The patient described the issue as a rash. Reported duration is less than one week. The subject is a male aged 50–59. The patient indicates the lesion is fluid-filled, raised or bumpy and rough or flaky. Symptoms reported: pain and burning. The patient indicates associated fatigue. Close-up view: 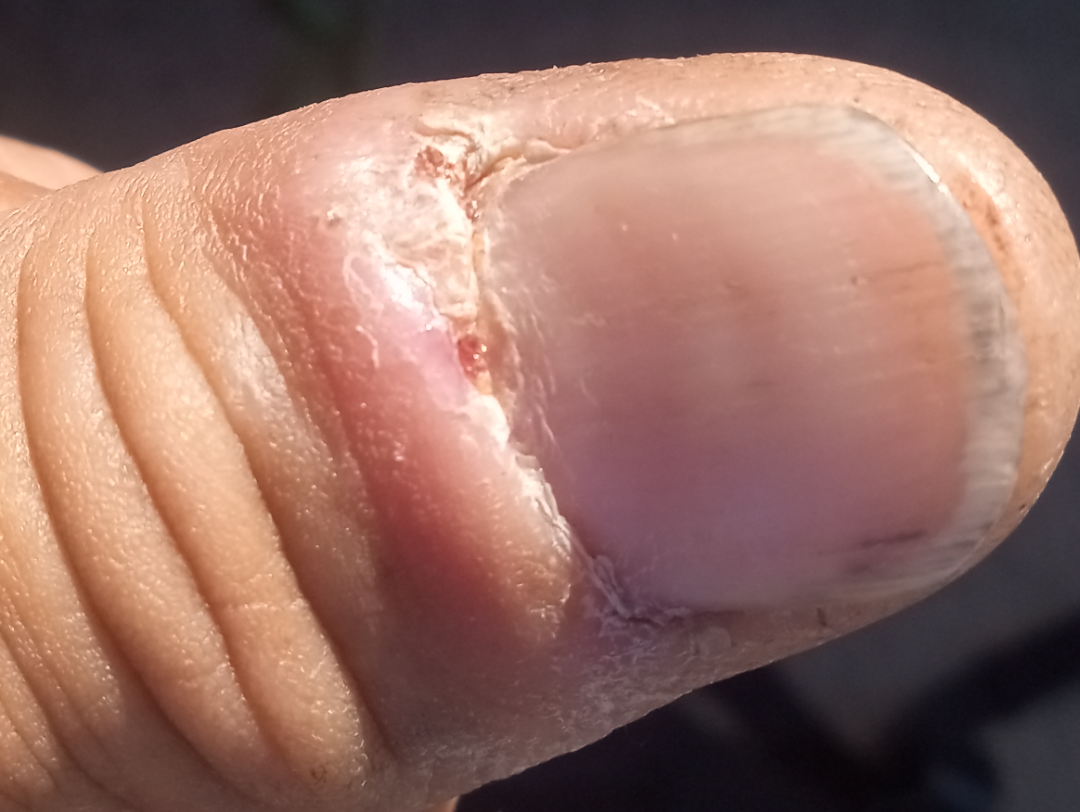On remote review of the image, in keeping with Paronychia.